The photograph was taken at a distance · located on the top or side of the foot and leg — 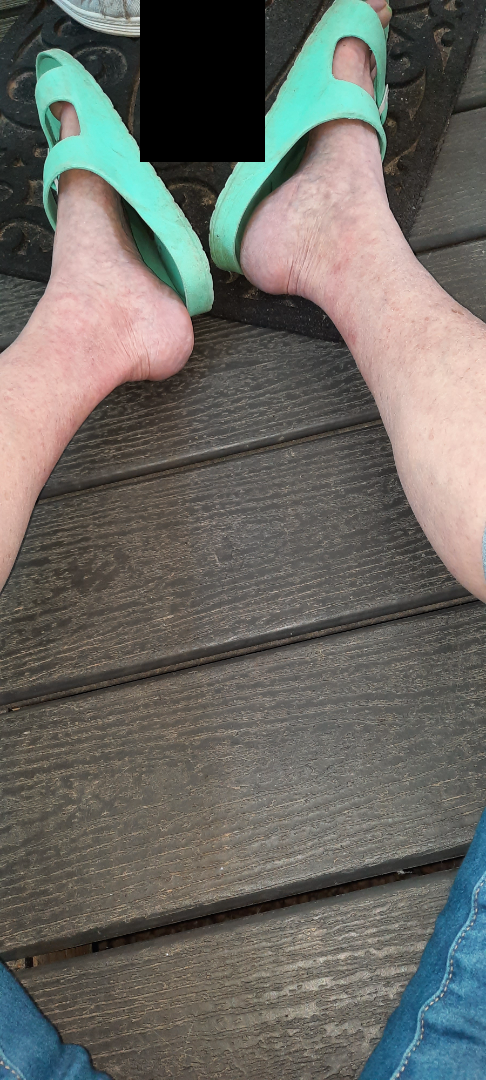Review: The case was indeterminate on photographic review. Patient information: Texture is reported as raised or bumpy. The patient considered this skin that appeared healthy to them. The condition has been present for more than one year. The lesion is associated with itching, pain, bothersome appearance and enlargement.